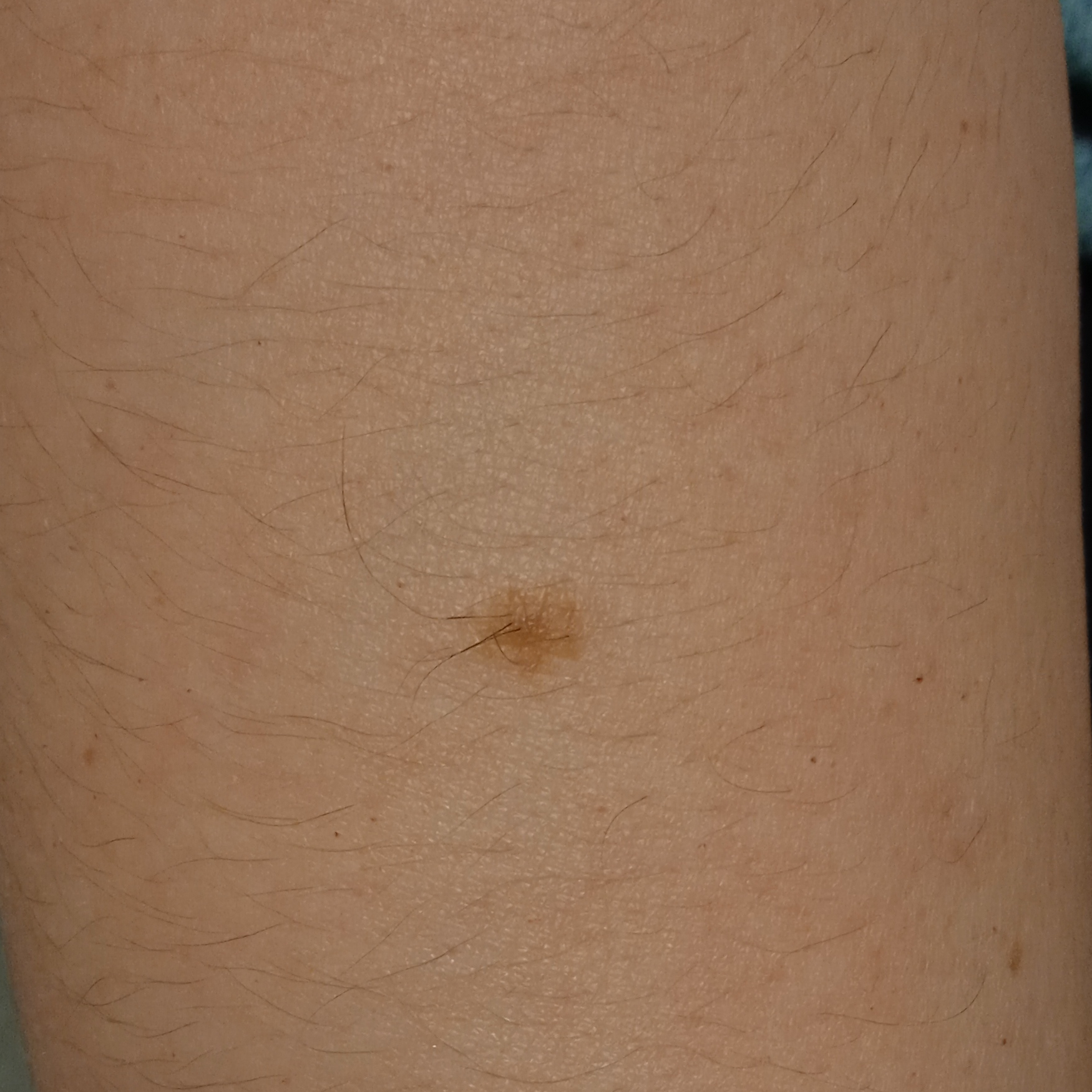{"sun_reaction": "skin reddens painfully with sun exposure", "mole_burden": "a moderate number of melanocytic nevi", "image": "clinical photograph", "referral": "research study (no referral diagnosis)", "patient": {"age": 35, "sex": "female"}, "lesion_location": "an arm", "lesion_size": {"diameter_mm": 5.8}, "diagnosis": {"name": "melanocytic nevus", "malignancy": "benign"}}